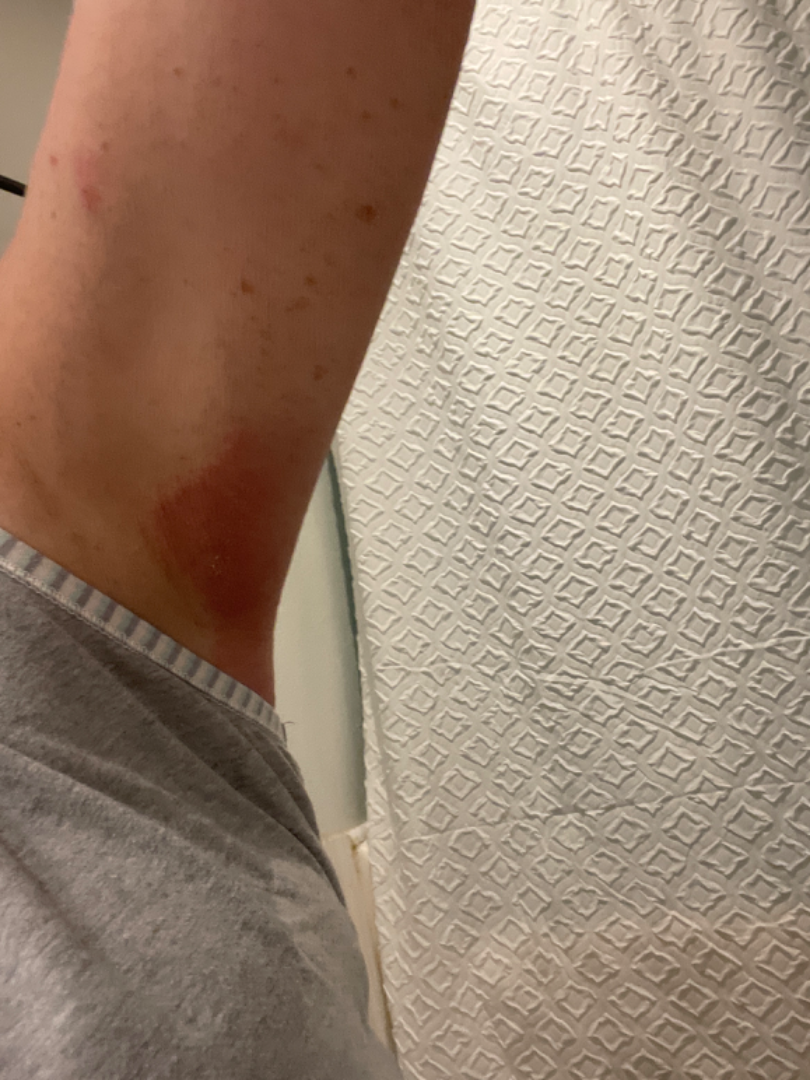Cellulitis (most likely); Urticaria (possible); Inflammatory dermatosis (possible).